A dermoscopic photograph of a skin lesion.
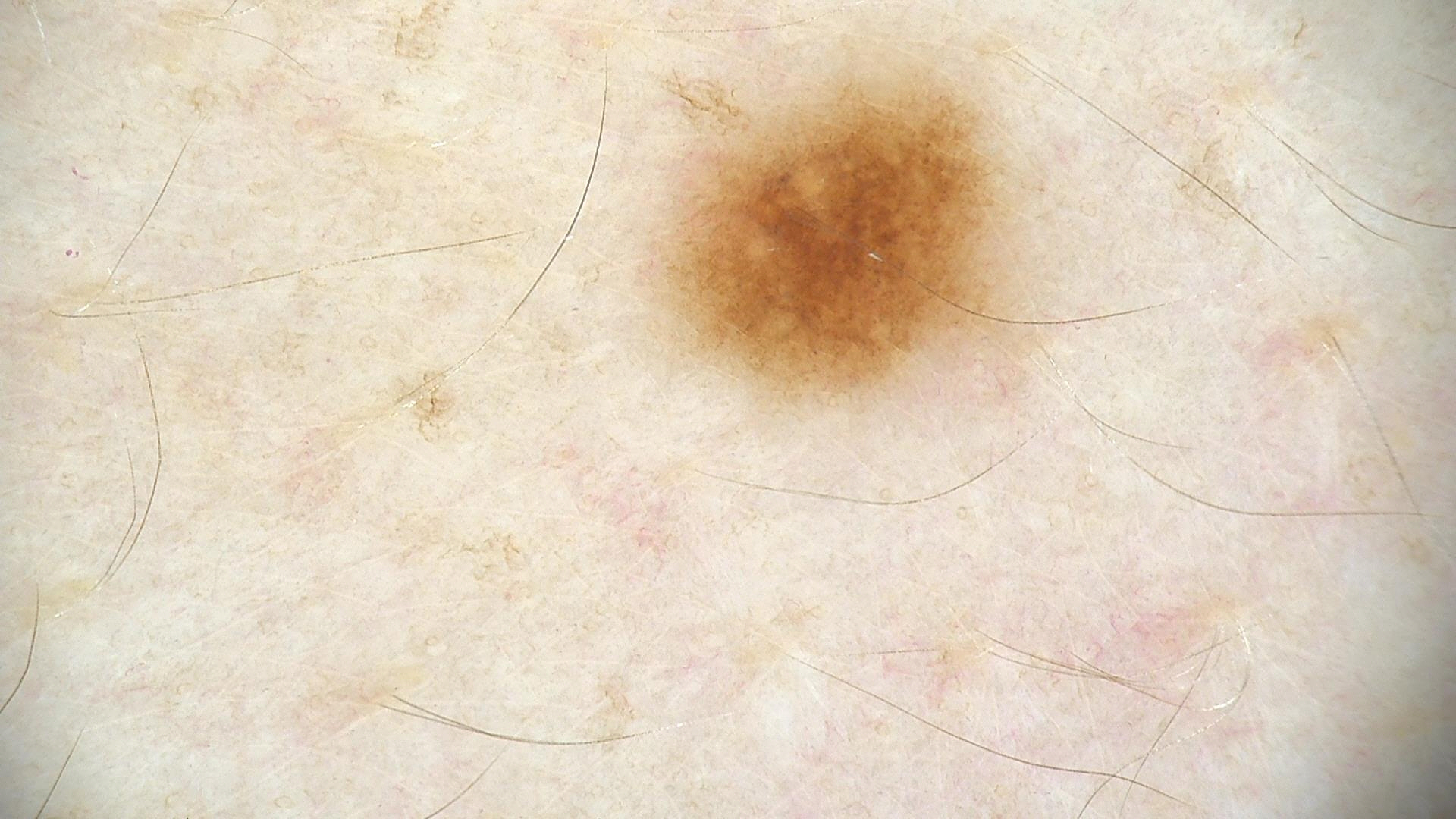Conclusion: Classified as a benign lesion — a dysplastic junctional nevus.